A clinical photo of a skin lesion taken with a smartphone: 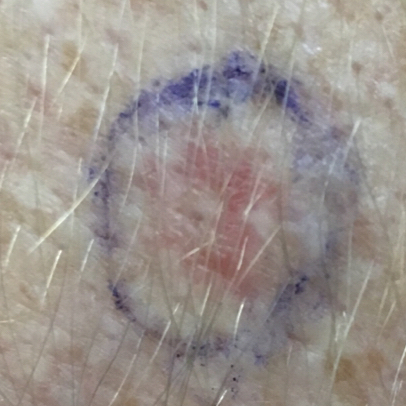body site: an arm; reported symptoms: itching; diagnosis: actinic keratosis (biopsy-proven).